A skin lesion imaged with a dermatoscope.
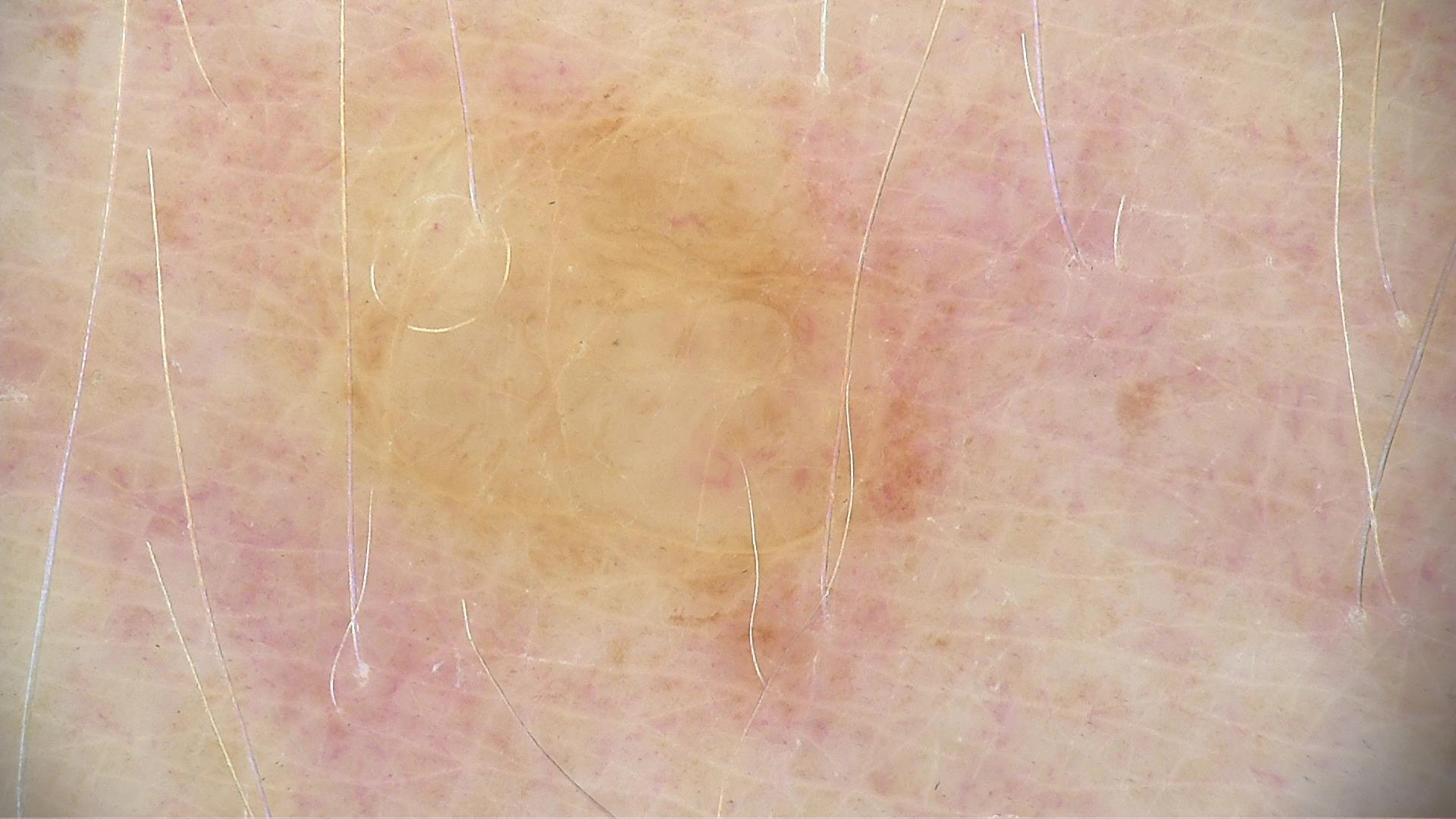- class — dermal nevus (expert consensus)